This is a close-up image. The lesion is described as raised or bumpy. Self-categorized by the patient as a rash. Reported duration is one to four weeks. Reported lesion symptoms include bothersome appearance, pain and itching. The front of the torso and back of the torso are involved. Associated systemic symptoms include fatigue. Female contributor, age 50–59.
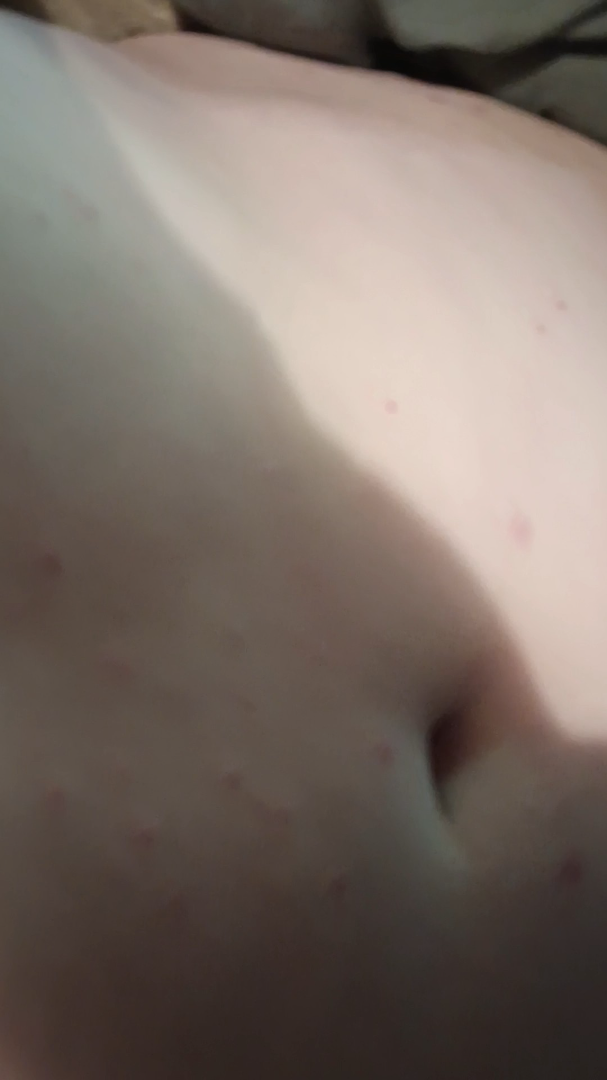Assessment:
No differential diagnosis could be assigned on photographic review.